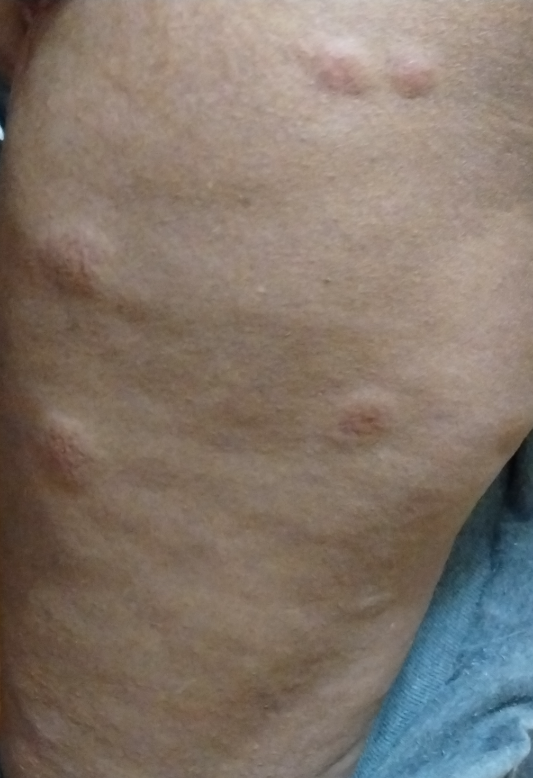assessment: not assessable